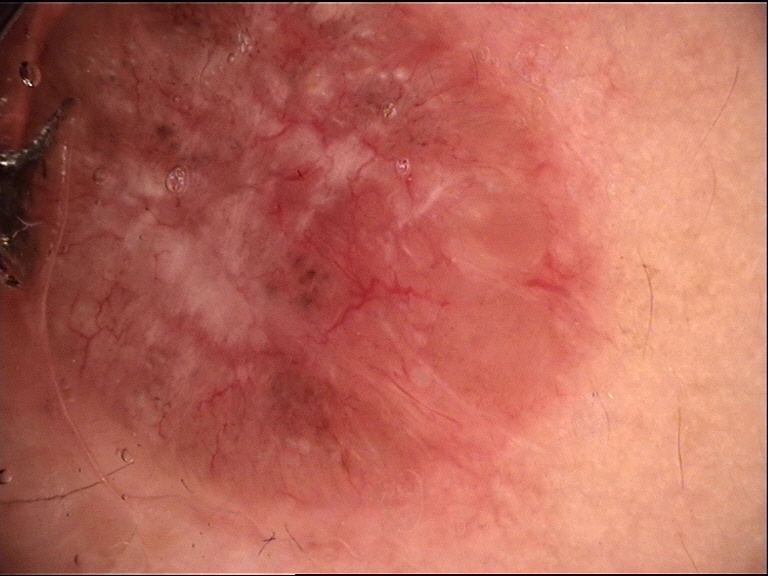Findings: A dermoscopy image of a single skin lesion. Conclusion: The biopsy diagnosis was a malignant, keratinocytic lesion — a basal cell carcinoma.